A skin lesion imaged with a dermatoscope:
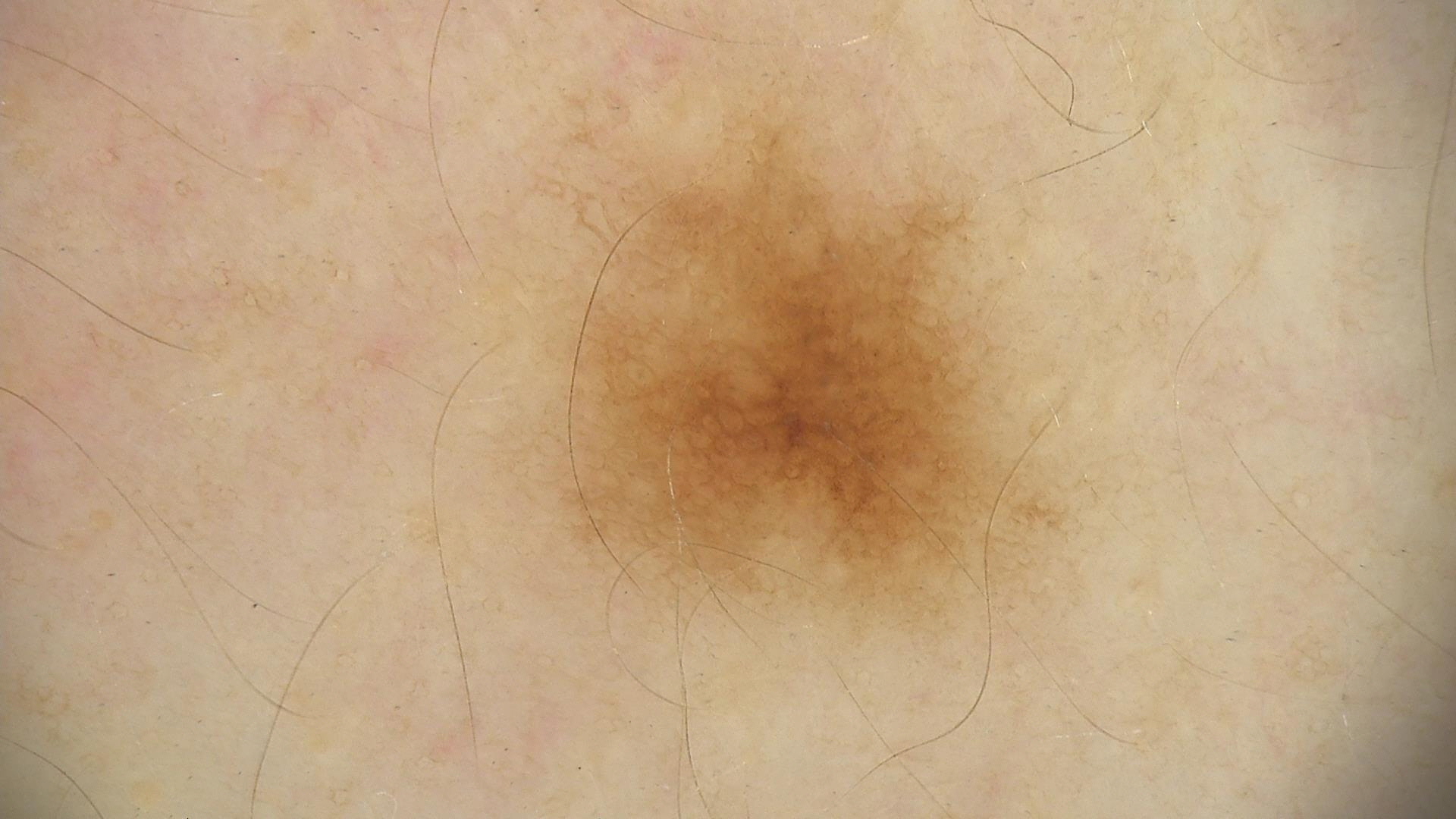Consistent with a dysplastic junctional nevus.